A dermatoscopic image of a skin lesion: 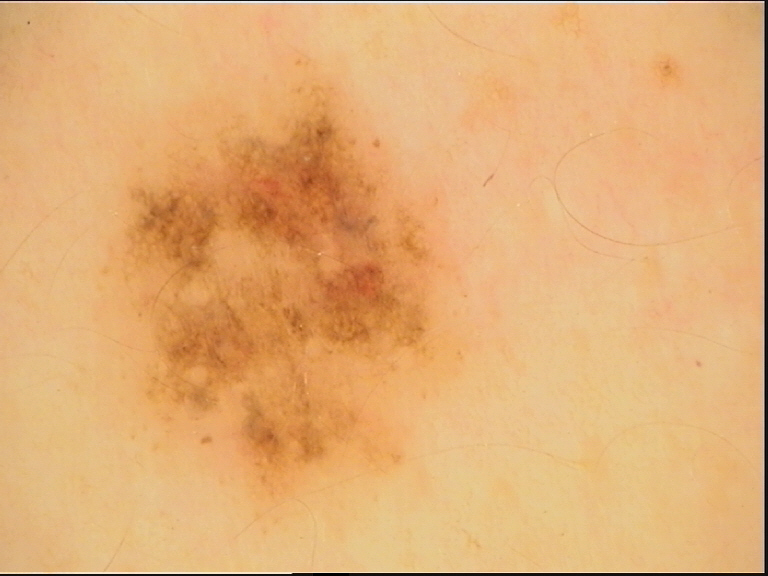class = dysplastic junctional nevus (expert consensus)